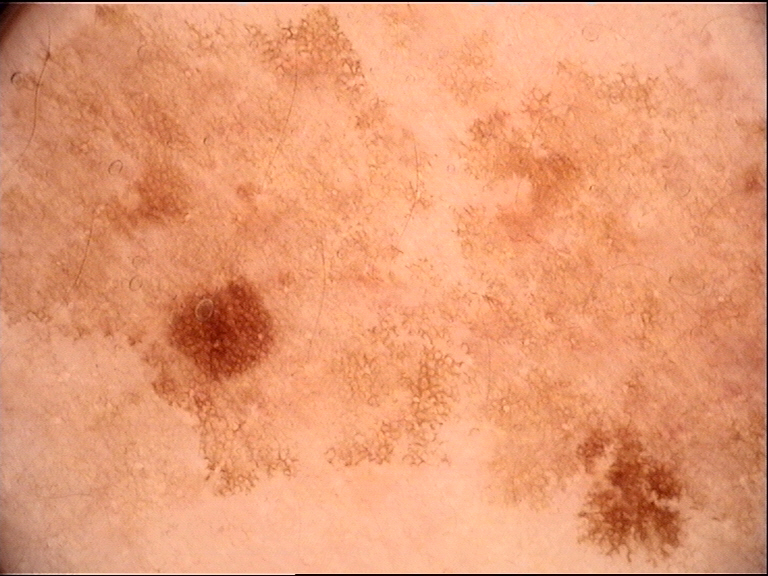Impression: Classified as a solar lentigo.